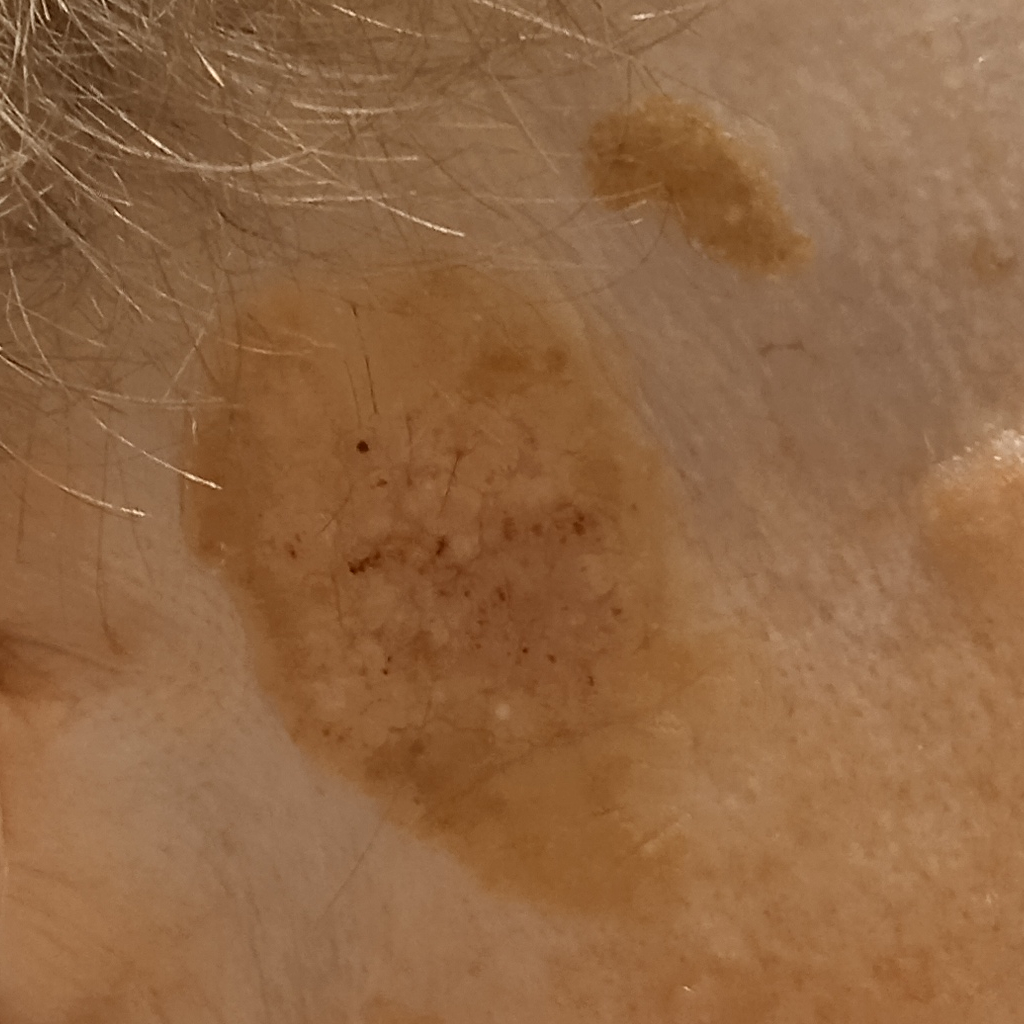Conclusion: The consensus diagnosis for this lesion was a seborrheic keratosis.